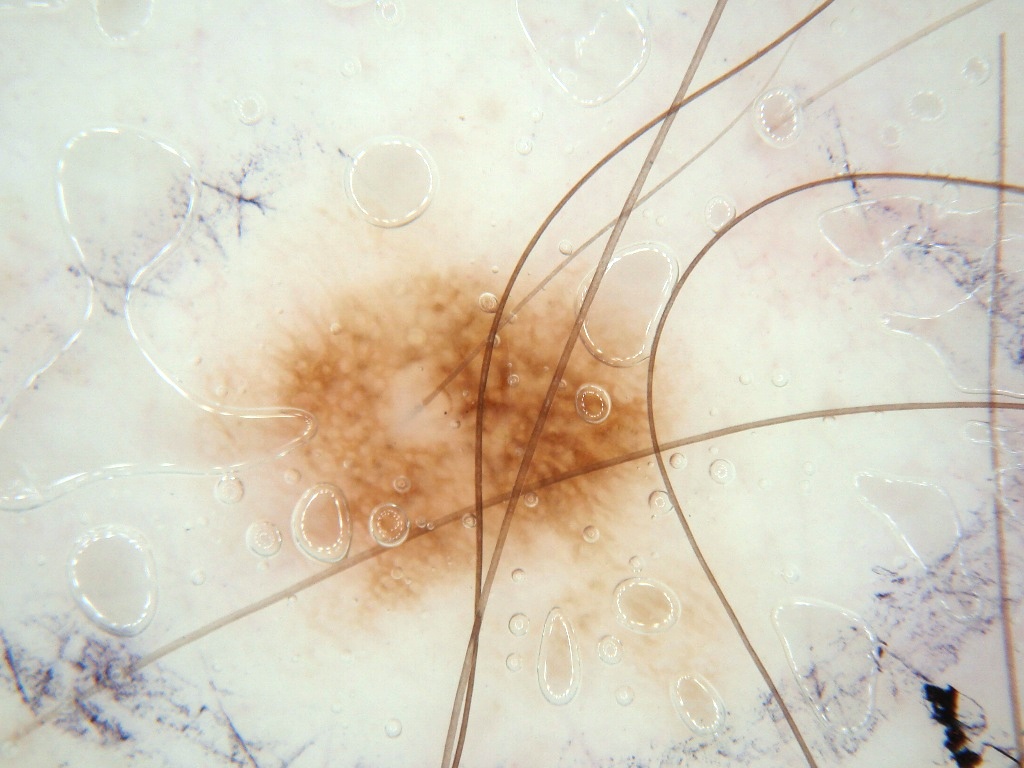{
  "image": {
    "modality": "dermoscopy"
  },
  "lesion_location": {
    "bbox_xyxy": [
      193,
      250,
      737,
      715
    ]
  },
  "diagnosis": {
    "malignancy": "benign",
    "provenance": "clinical"
  }
}